A dermoscopic photograph of a skin lesion.
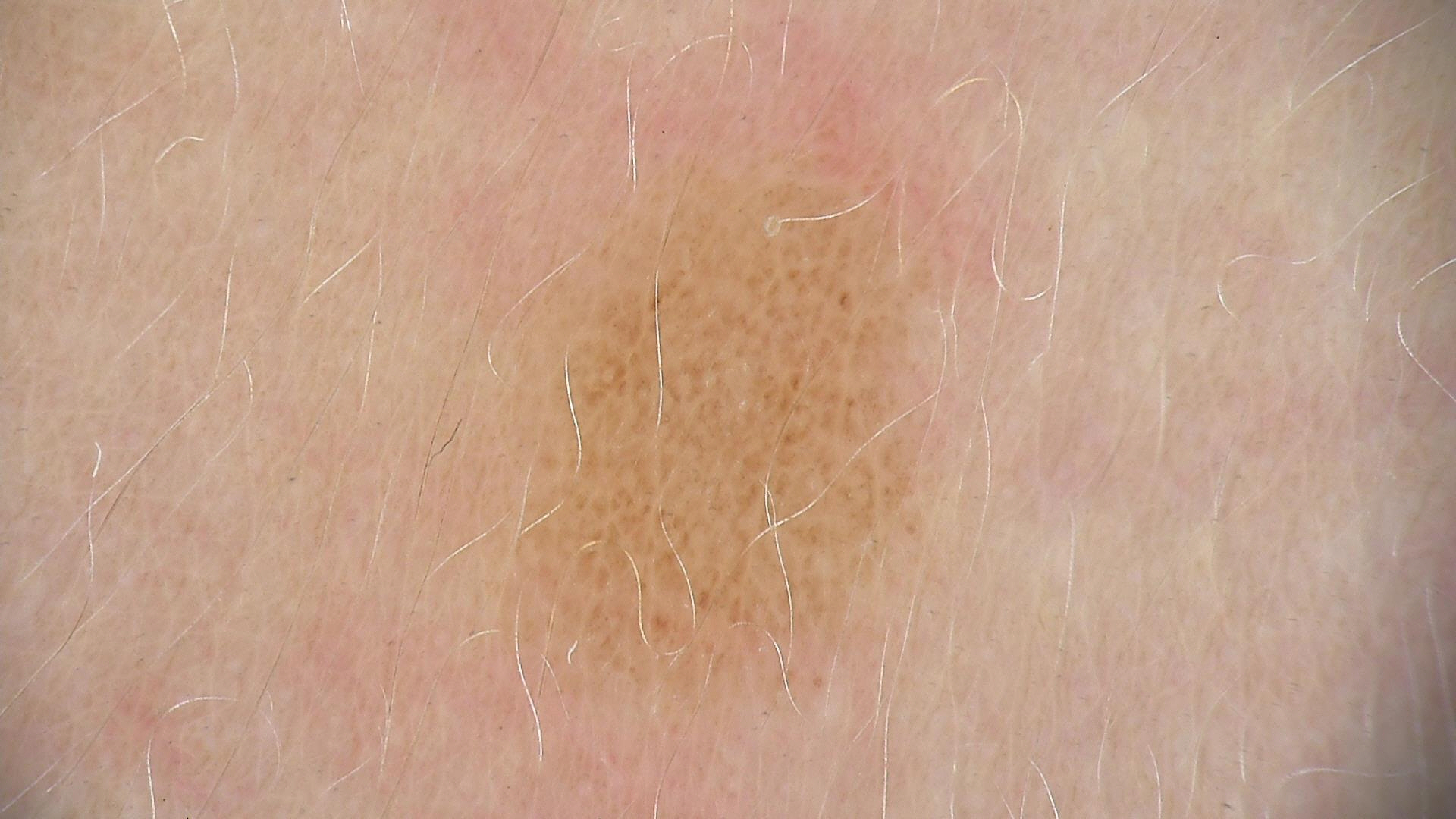Q: What is the diagnosis?
A: dysplastic junctional nevus (expert consensus)